This is a close-up image. The contributor is 50–59, female: 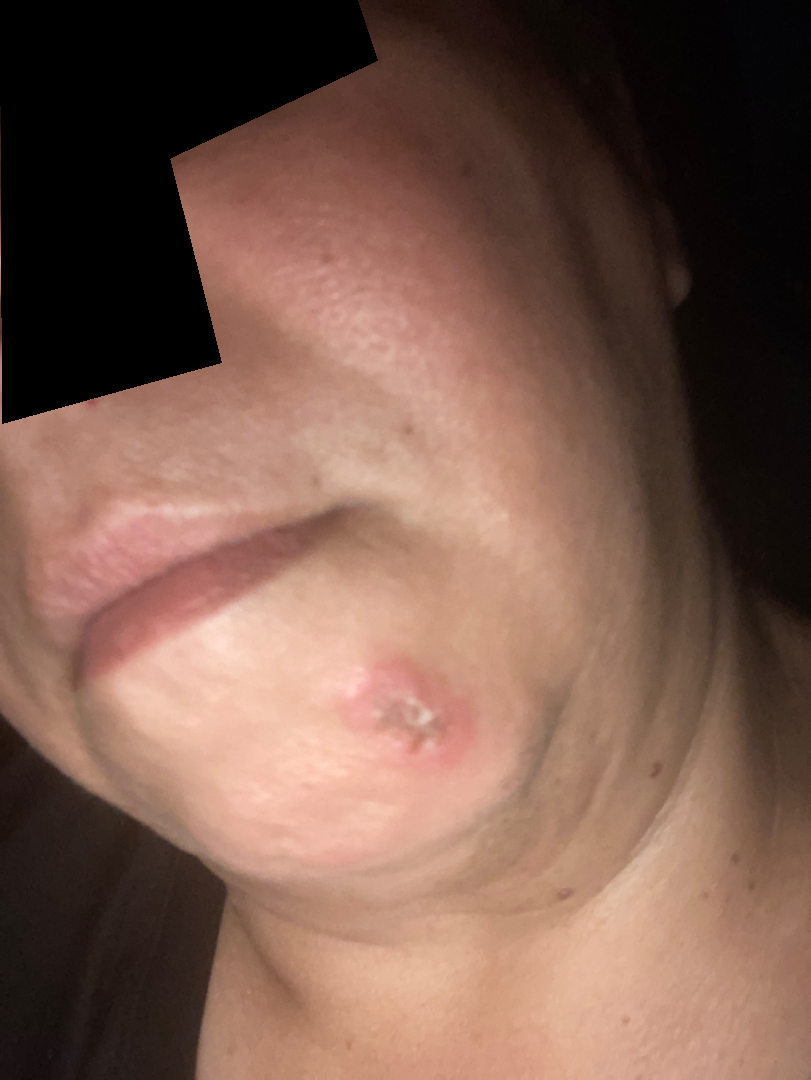Findings: Single-reviewer assessment: Abscess, skin cyst and Odontogenic keratocyst were considered with similar weight.